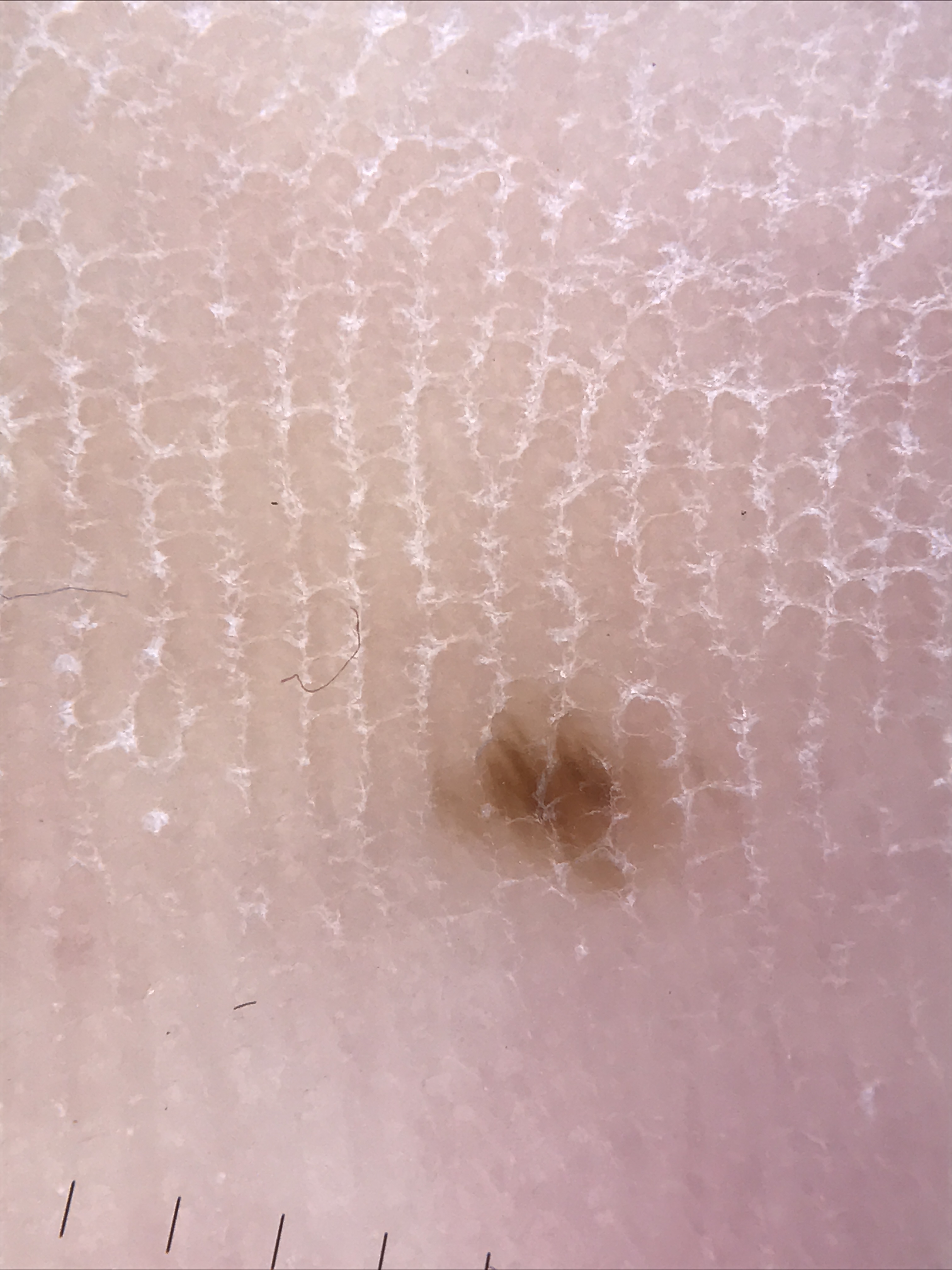diagnosis:
  name: acral junctional nevus
  code: ajb
  malignancy: benign
  super_class: melanocytic
  confirmation: expert consensus